A dermoscopy image of a single skin lesion: 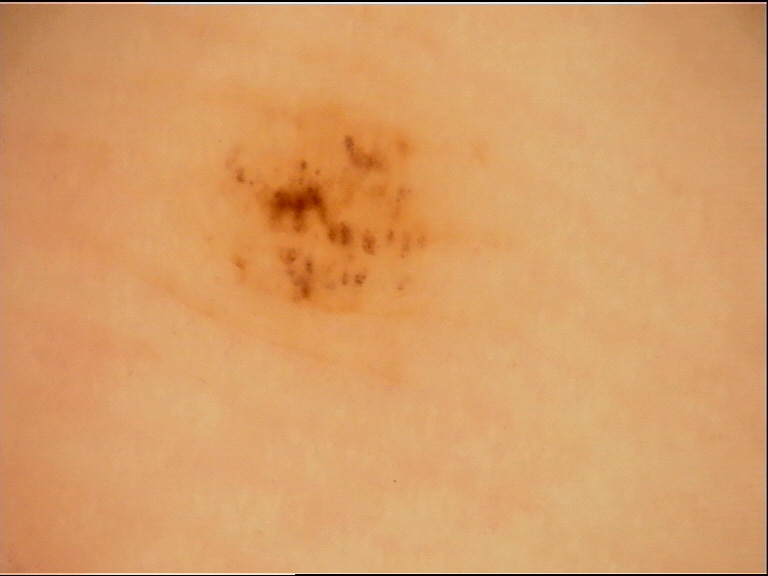This is a banal lesion. Diagnosed as an acral junctional nevus.